A wide-field clinical photograph of a skin lesion. Fitzpatrick II. A female subject aged 68 to 72.
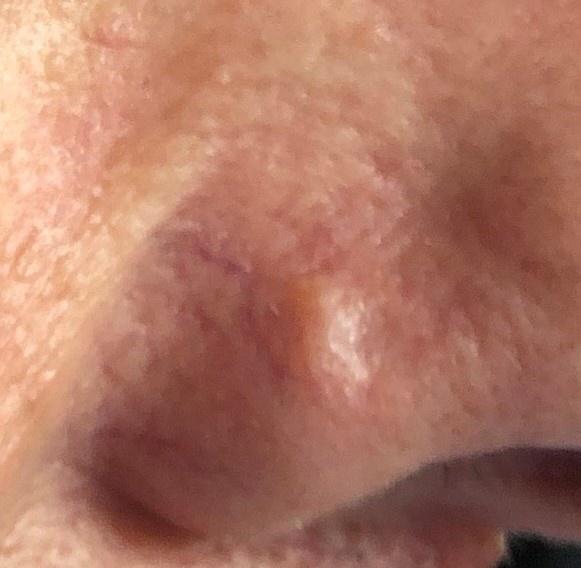| key | value |
|---|---|
| body site | the head or neck |
| diagnosis | Basal cell carcinoma (biopsy-proven) |